The photograph is a close-up of the affected area; located on the front of the torso — 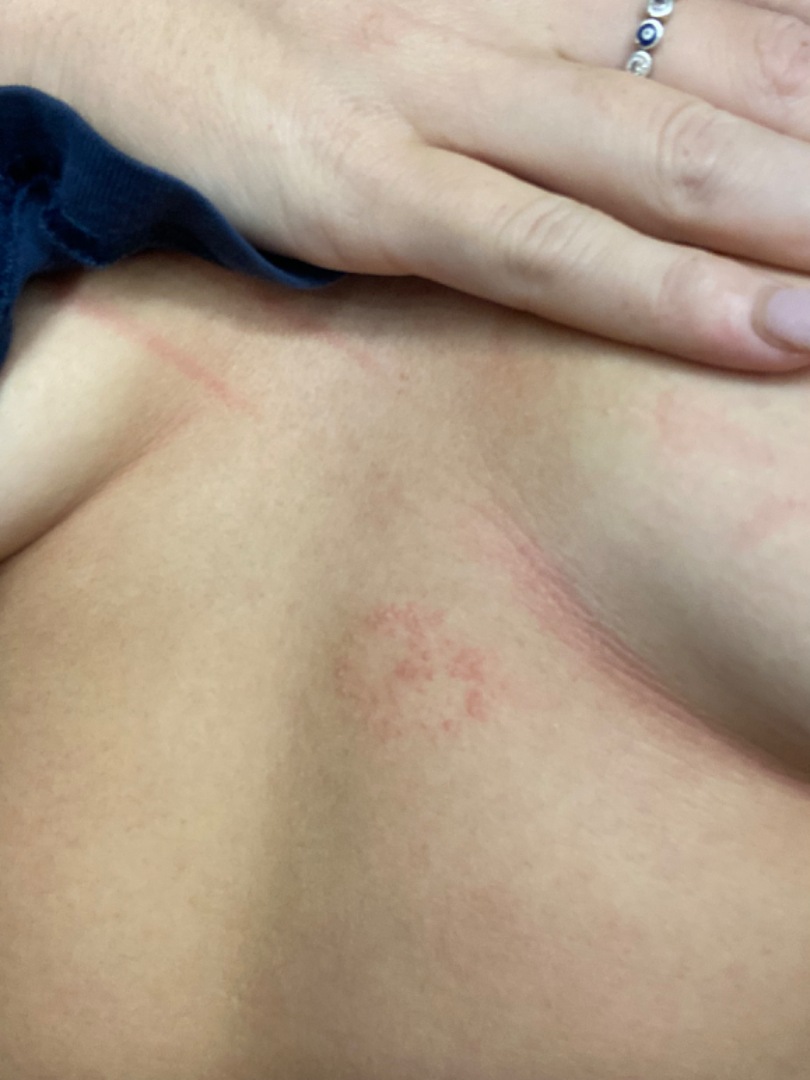The patient indicates bothersome appearance. Texture is reported as raised or bumpy. On photographic review: most consistent with Tinea; the differential also includes Eczema; possibly Irritant Contact Dermatitis.